A dermoscopic image of a skin lesion.
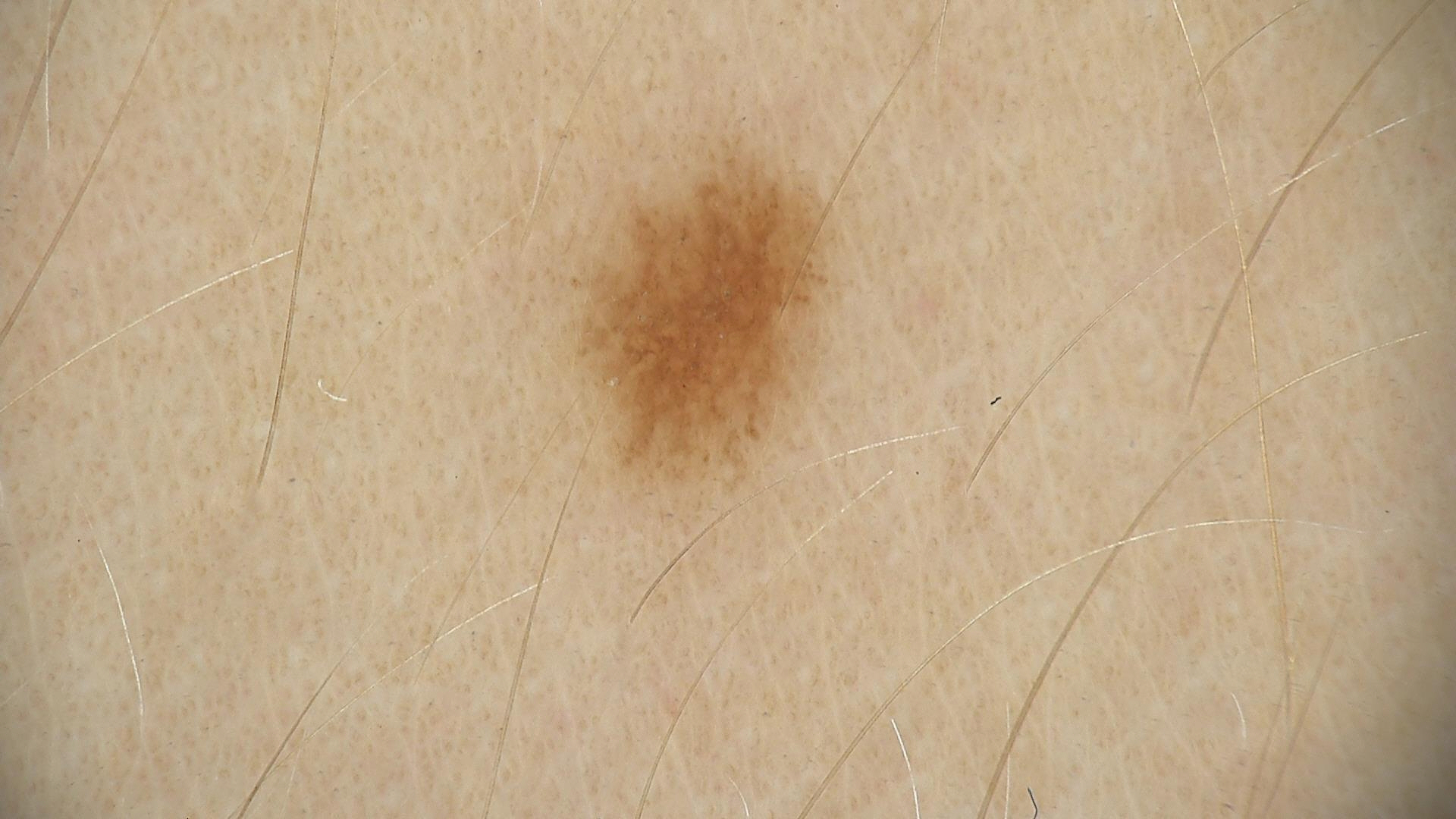Labeled as a benign lesion — a dysplastic junctional nevus.